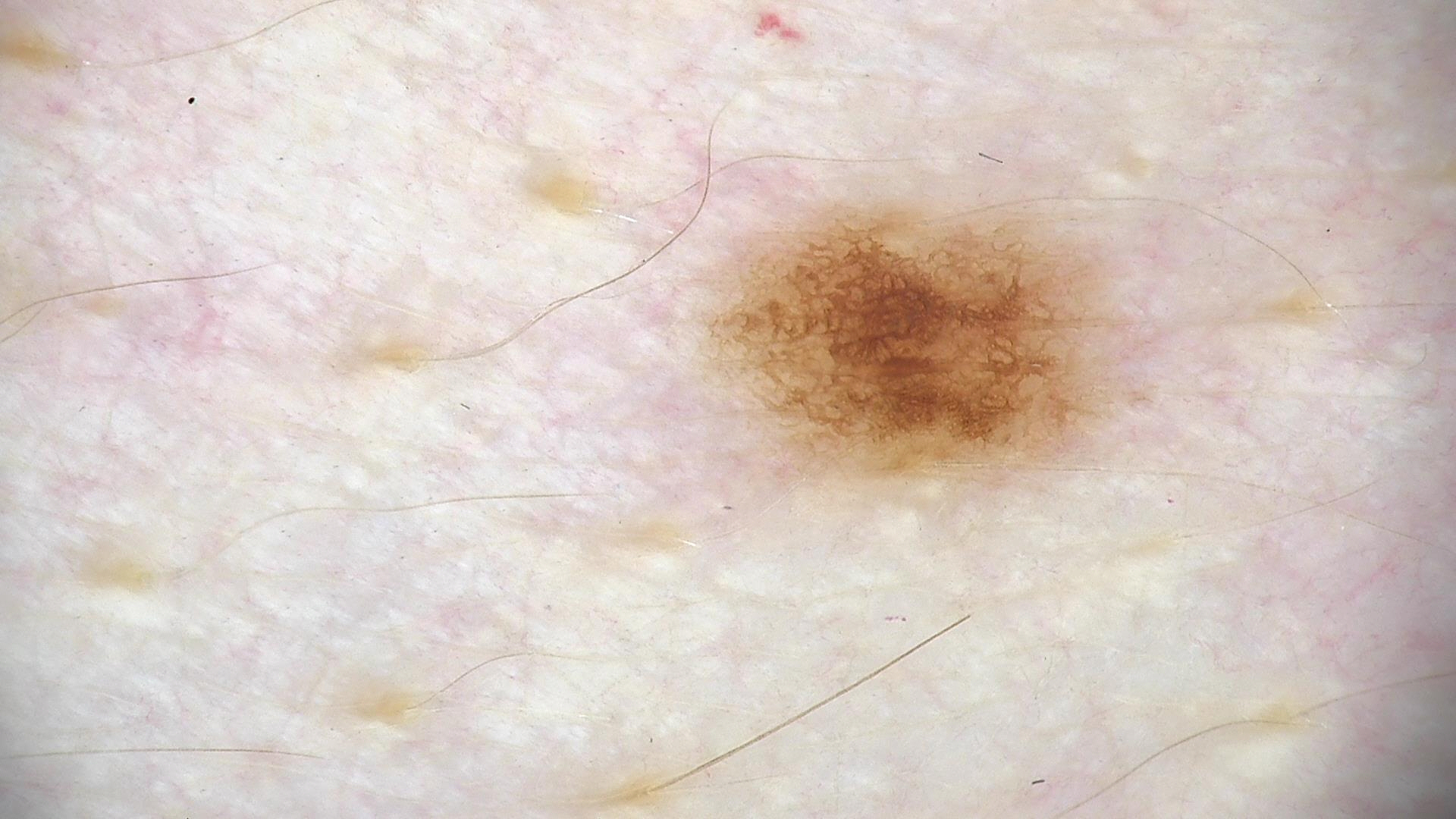Findings:
* modality: dermatoscopy
* diagnosis: dysplastic junctional nevus (expert consensus)